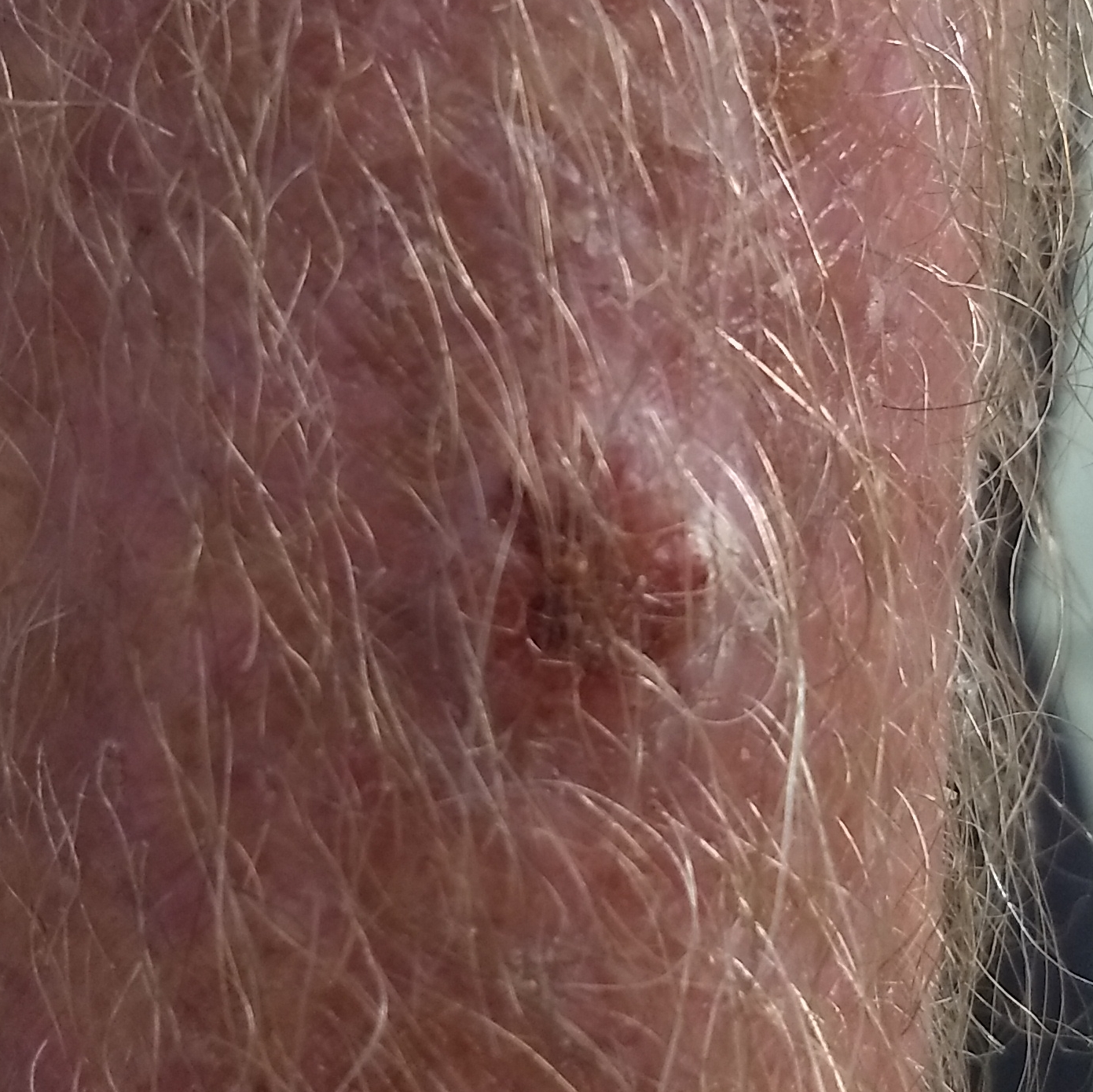Q: Tell me about the patient.
A: male, in their early 70s
Q: What kind of image is this?
A: clinical photo
Q: What is the patient's skin type?
A: II
Q: What are the relevant risk factors?
A: alcohol use, pesticide exposure, prior skin cancer (patient or family), prior malignancy (patient or family)
Q: What is the anatomic site?
A: a forearm
Q: How large is the lesion?
A: 10 × 8 mm
Q: What symptoms does the patient report?
A: bleeding, pain, elevation, itching
Q: What did the workup show?
A: basal cell carcinoma (biopsy-proven)